Recorded as Fitzpatrick skin type II; a skin lesion imaged with contact-polarized dermoscopy; a male subject roughly 55 years of age; per the chart, a previous melanoma but no first-degree relative with melanoma — 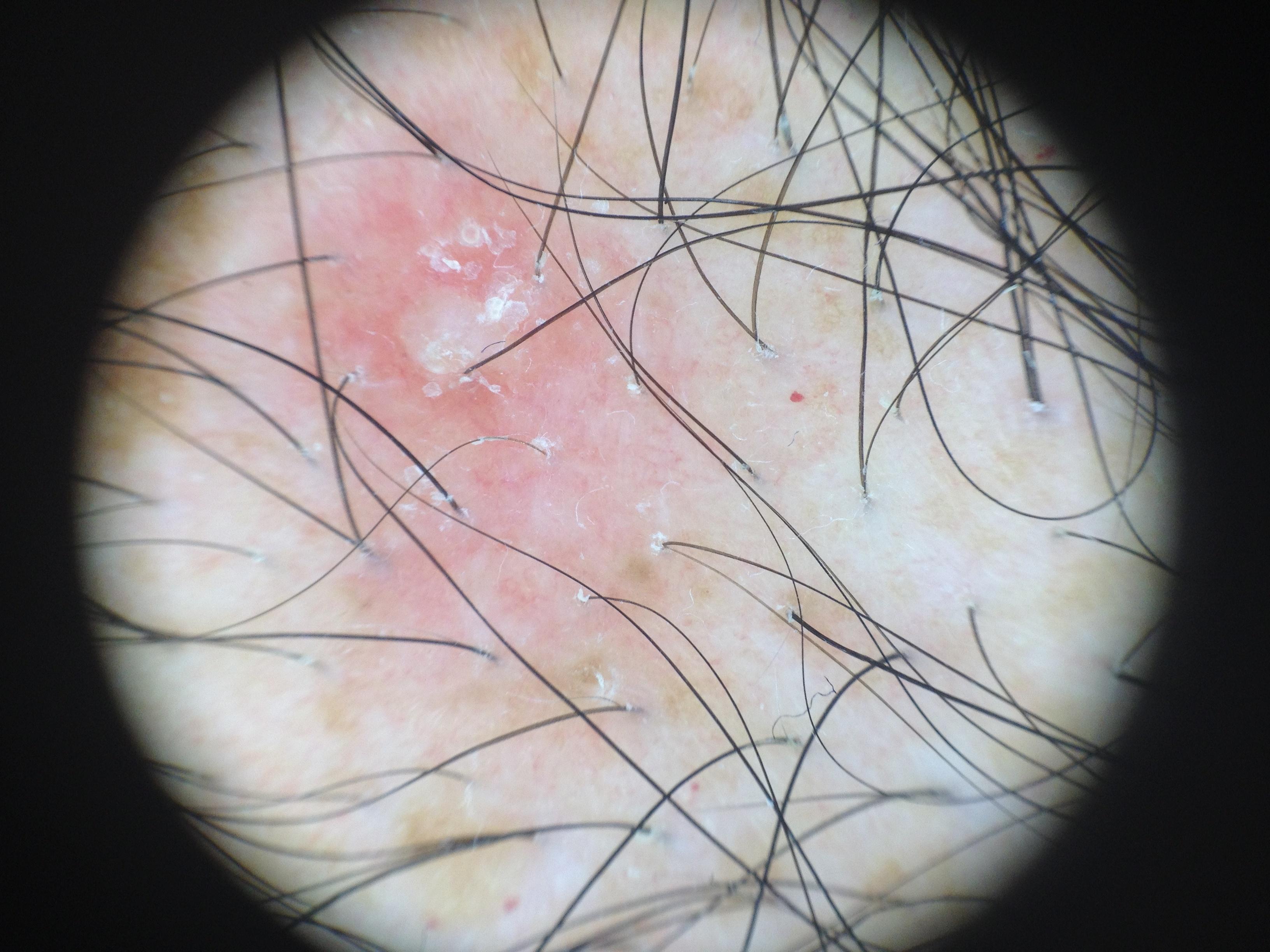site = the trunk (the posterior trunk) | diagnosis = Solar or actinic keratosis (clinical impression).